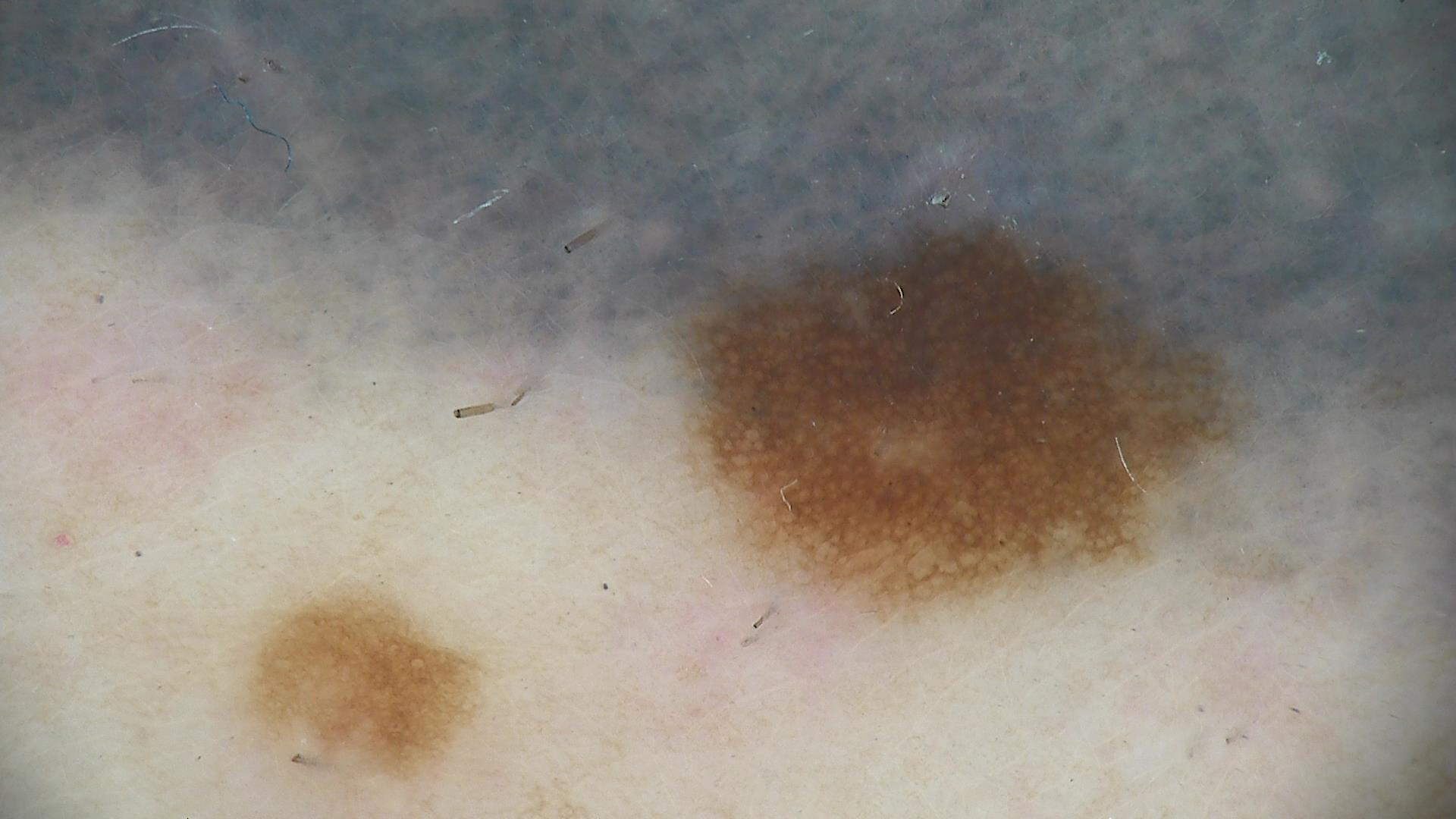imaging — dermatoscopy
class — dysplastic junctional nevus (expert consensus)